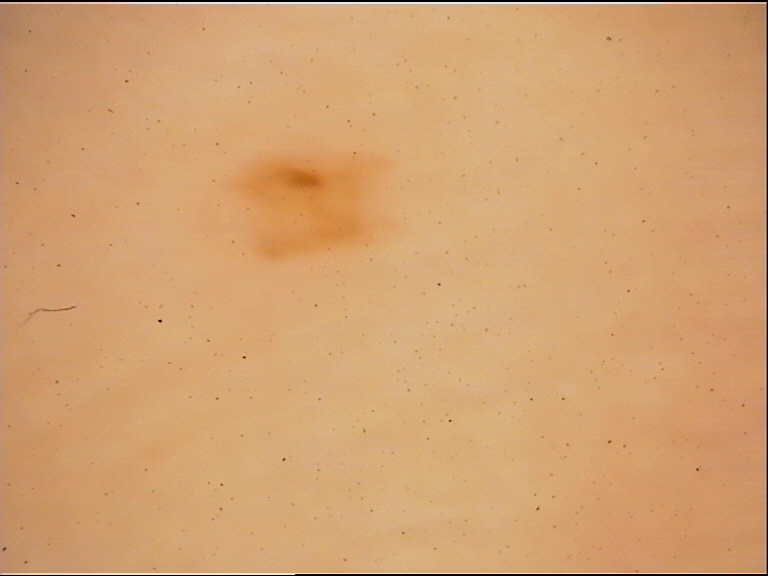modality = dermoscopy; label = acral junctional nevus (expert consensus).